The lesion is associated with bothersome appearance, itching and enlargement. The patient notes the lesion is raised or bumpy. The subject is 30–39, female. A close-up photograph. No associated systemic symptoms reported. Reported duration is about one day. The affected area is the leg. Fitzpatrick III; lay graders estimated MST 2–3: 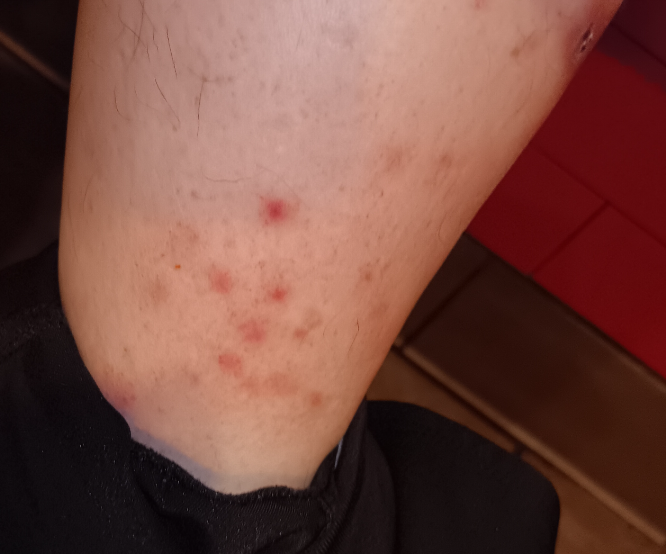| feature | finding |
|---|---|
| assessment | indeterminate from the photograph |